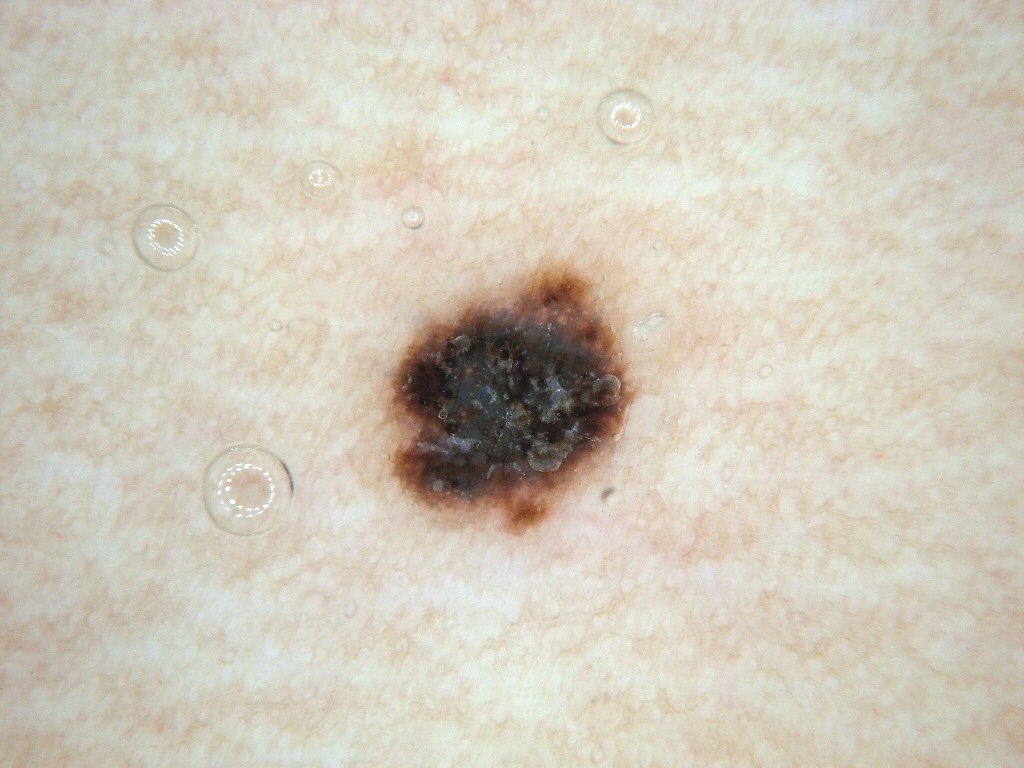Summary:
A dermatoscopic image of a skin lesion. The lesion is located at left=376, top=268, right=636, bottom=533. Dermoscopic assessment notes no globules or streaks.
Assessment:
Diagnosed as a benign skin lesion.